A dermoscopic image of a skin lesion:
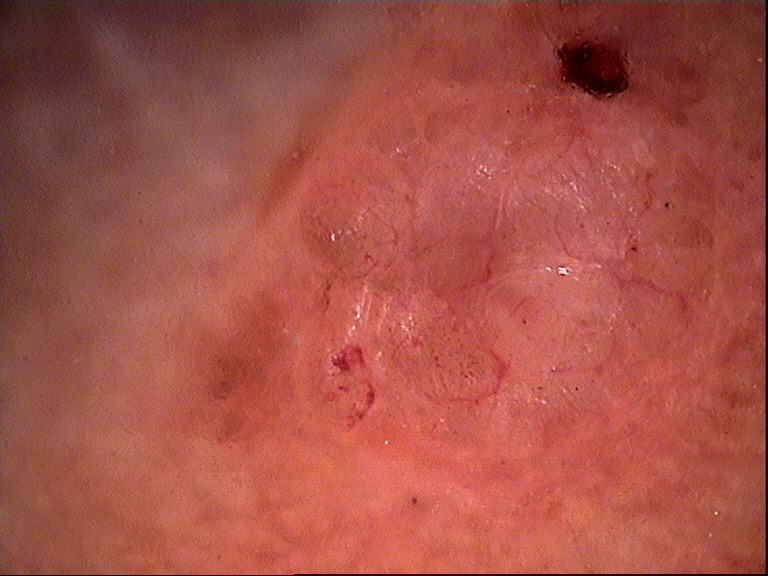Q: What is the diagnosis?
A: basal cell carcinoma (biopsy-proven)